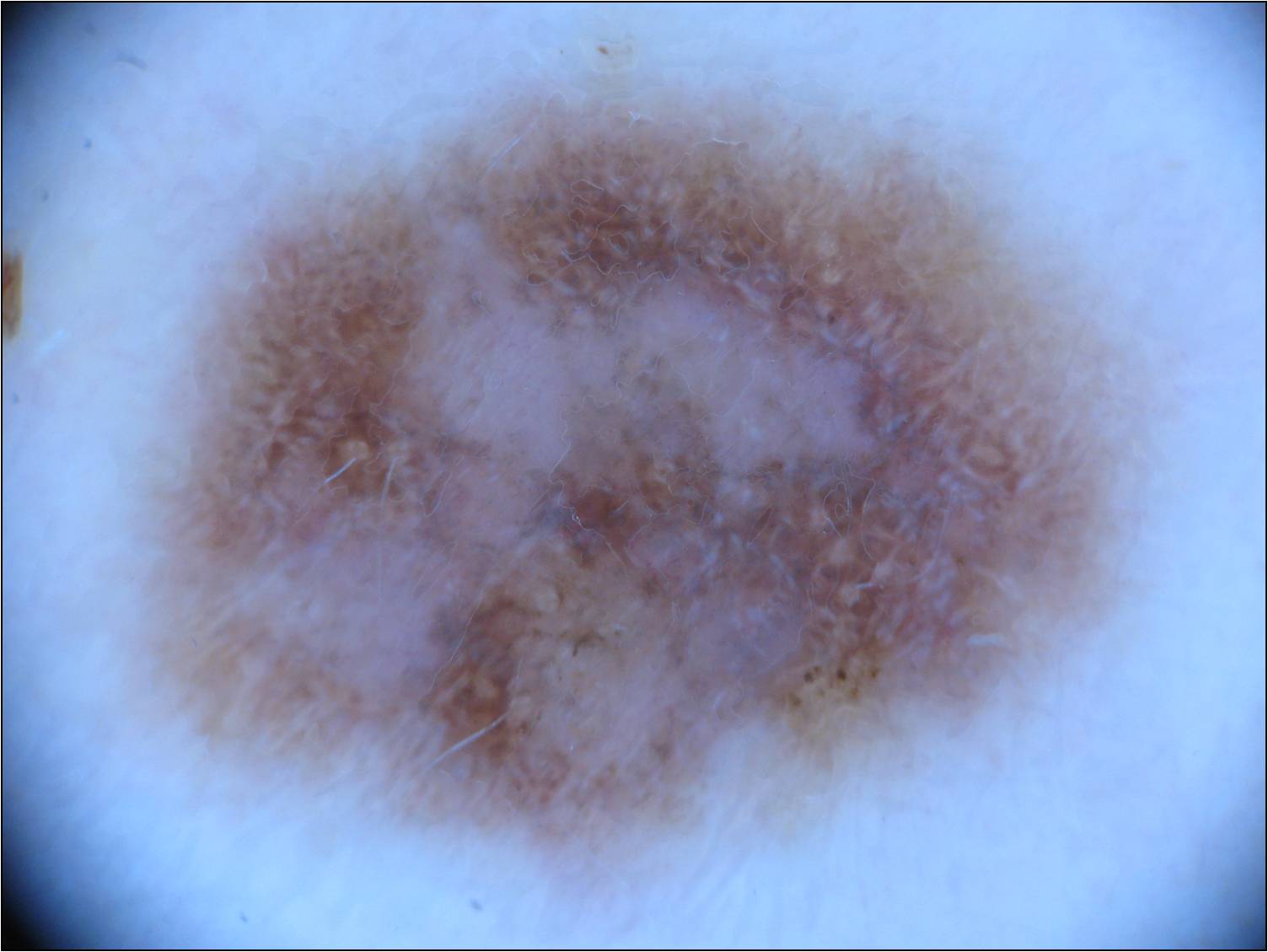{
  "image": {
    "modality": "dermoscopy"
  },
  "patient": {
    "sex": "female",
    "age_approx": 25
  },
  "lesion_extent": {
    "approx_field_fraction_pct": 46
  },
  "lesion_location": {
    "bbox_xyxy": [
      147,
      72,
      1116,
      852
    ]
  },
  "dermoscopic_features": {
    "present": [
      "globules"
    ],
    "absent": [
      "pigment network",
      "streaks",
      "milia-like cysts",
      "negative network"
    ]
  },
  "diagnosis": {
    "name": "melanoma",
    "malignancy": "malignant",
    "lineage": "melanocytic",
    "provenance": "histopathology"
  }
}